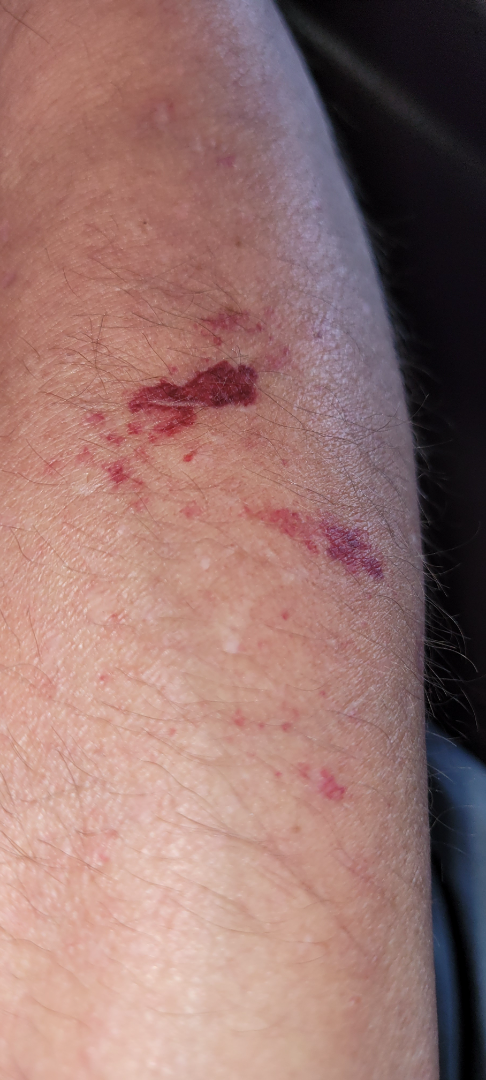image framing = at an angle | location = arm | patient = male, age 50–59 | impression = consistent with ecchymoses.